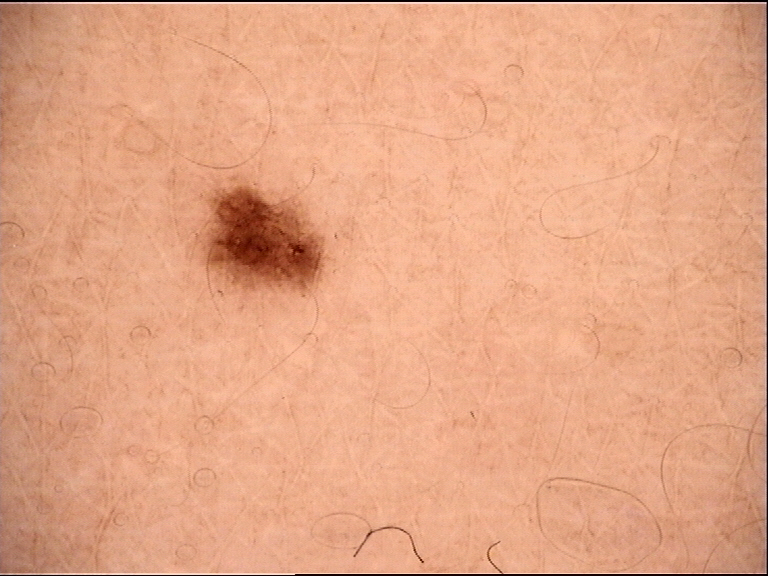Q: What is the diagnosis?
A: dysplastic junctional nevus (expert consensus)